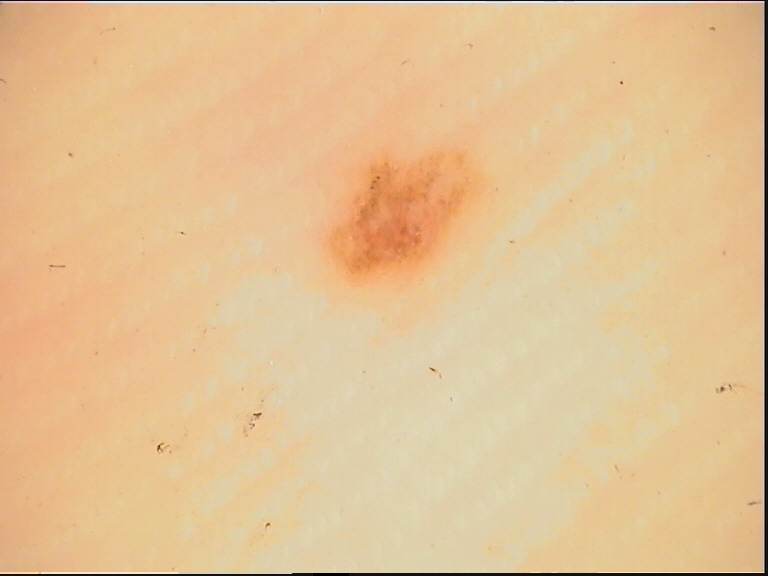assessment: acral dysplastic junctional nevus (expert consensus).